A dermatoscopic image of a skin lesion.
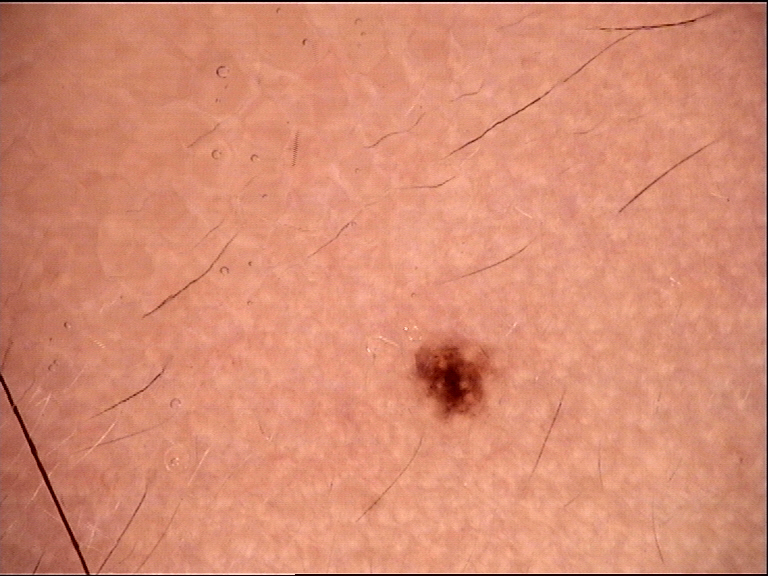The morphology is that of a banal, compound lesion.
Labeled as a Miescher nevus.